Fitzpatrick phototype II; history notes pesticide exposure, prior malignancy (patient or family), no alcohol use, and no prior skin cancer (patient or family); a male patient 46 years old: 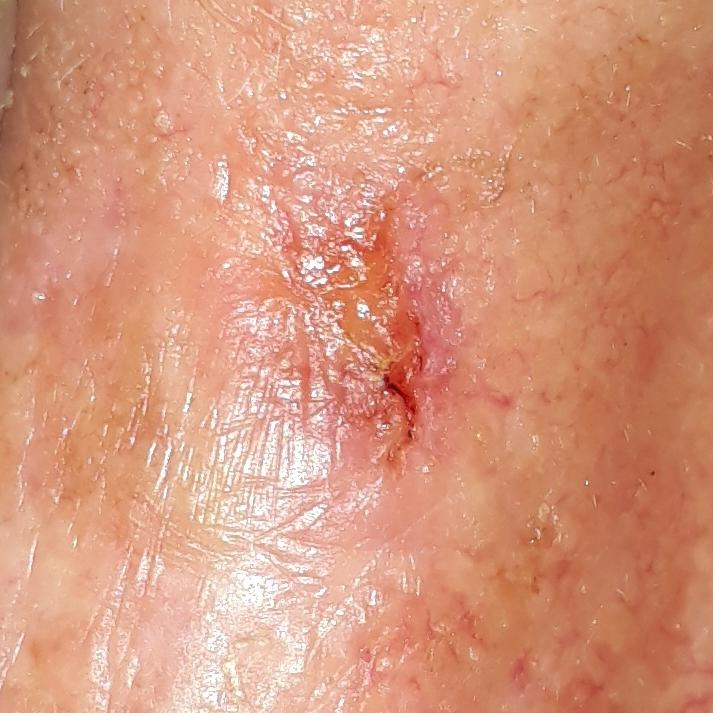Q: What is the anatomic site?
A: the nose
Q: How large is the lesion?
A: 6 × 4 mm
Q: What does the patient describe?
A: bleeding, pain, change in appearance, itching
Q: What did the workup show?
A: actinic keratosis (biopsy-proven)